A dermoscopic close-up of a skin lesion.
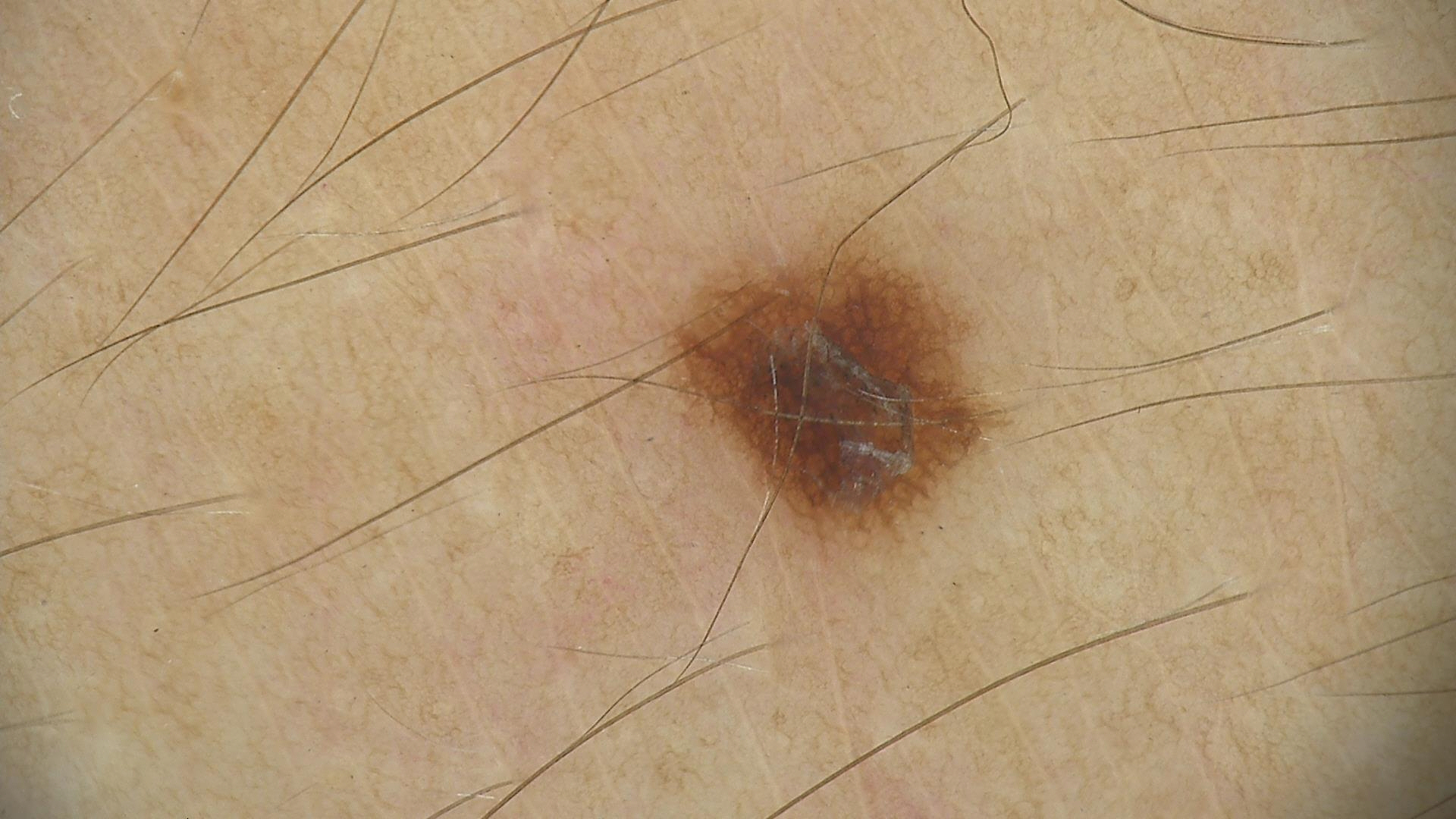Consistent with a benign lesion — a dysplastic junctional nevus.